A female patient 36 years of age. The patient is Fitzpatrick II. A clinical close-up photograph of a skin lesion:
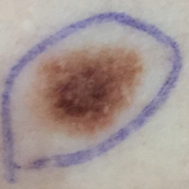Q: What is the diagnosis?
A: nevus (biopsy-proven)